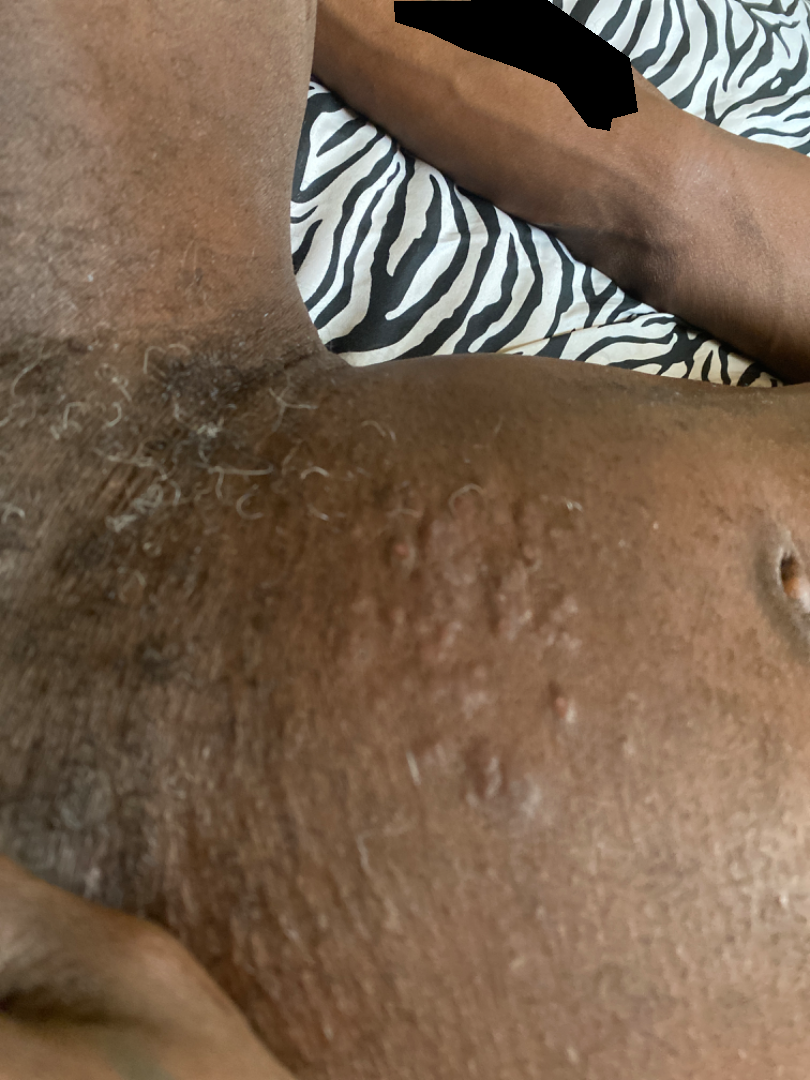An image taken at an angle.
Fitzpatrick skin type V; human graders estimated MST 6 or 8.
On remote review of the image, the leading impression is Allergic Contact Dermatitis; with consideration of Eczema; possibly Verruca vulgaris.